The lesion is described as raised or bumpy; an image taken at an angle; the subject is 40–49, female; present for less than one week; the affected area is the leg, head or neck and arm:
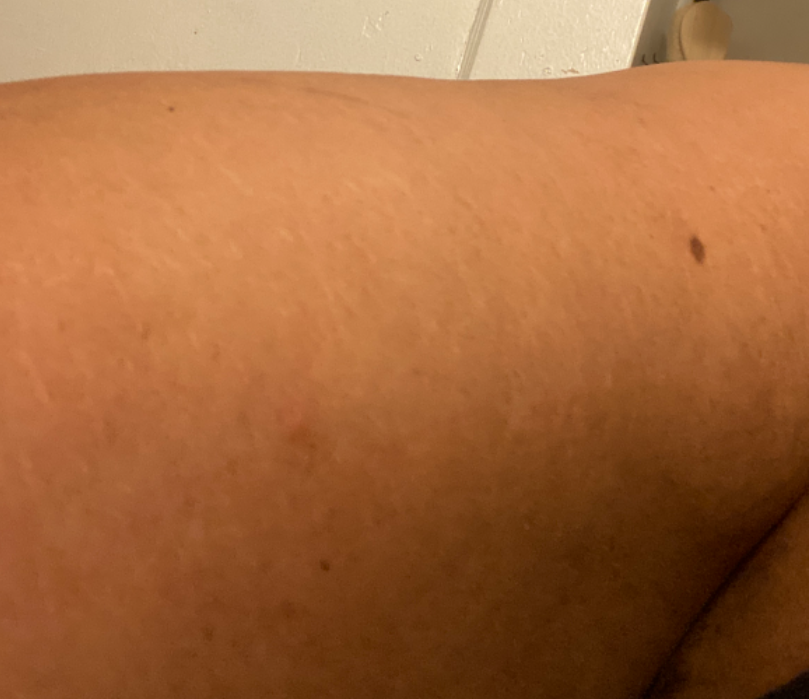Notes:
• diagnostic considerations · Acne and Folliculitis were each considered, in no particular order